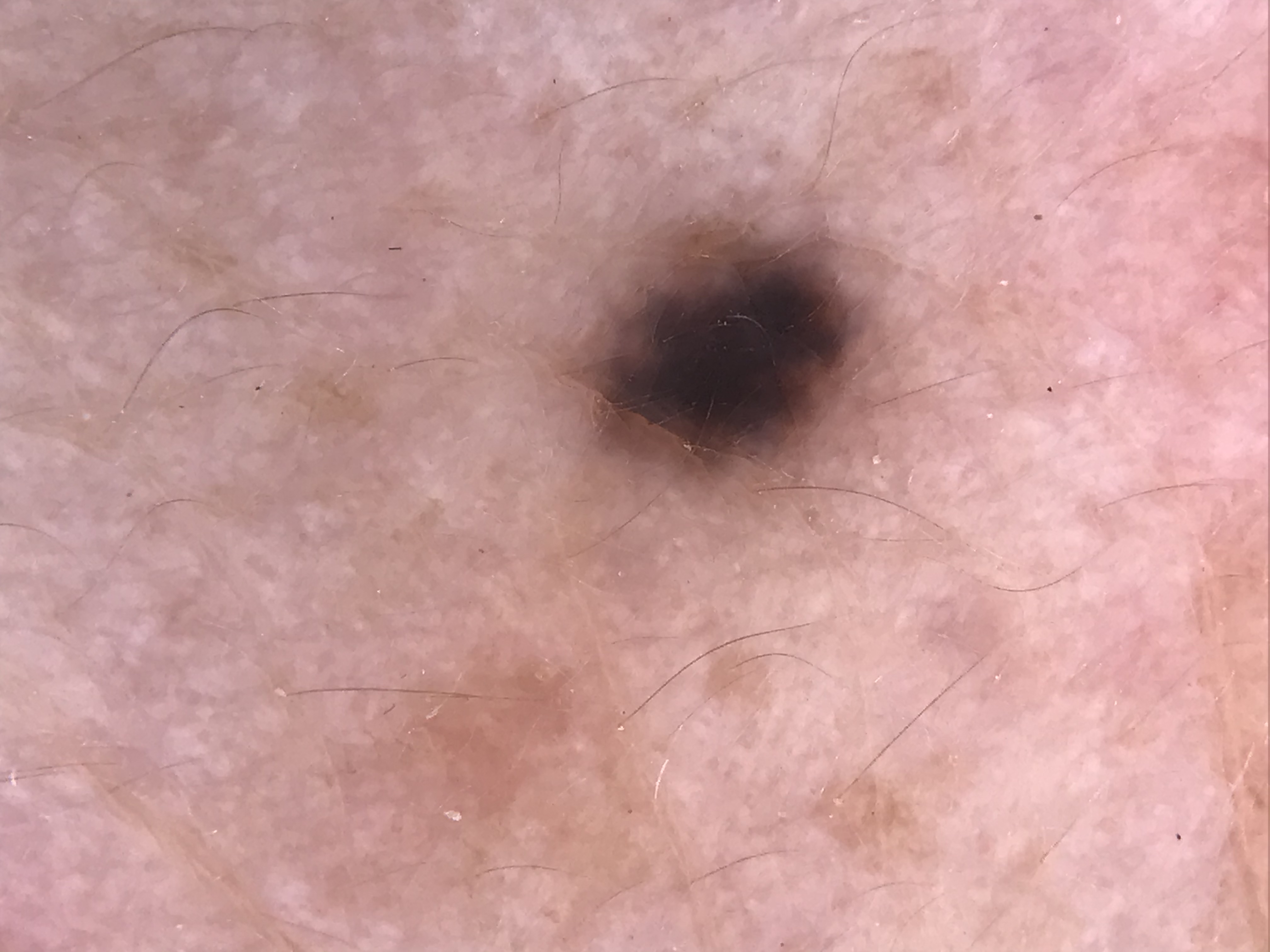Q: What is the imaging modality?
A: dermoscopy
Q: What is the lesion category?
A: banal, dermal
Q: What is the diagnosis?
A: blue nevus (expert consensus)